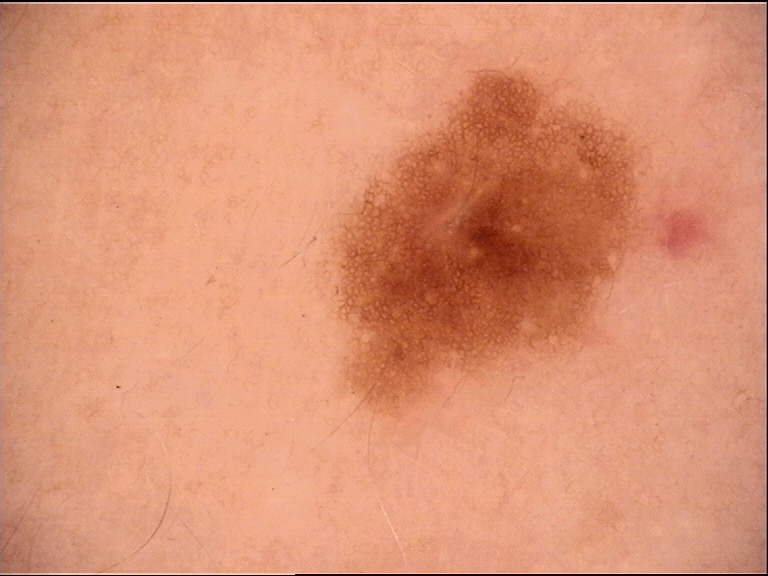  image: dermoscopy
  diagnosis:
    name: dysplastic junctional nevus
    code: jd
    malignancy: benign
    super_class: melanocytic
    confirmation: expert consensus